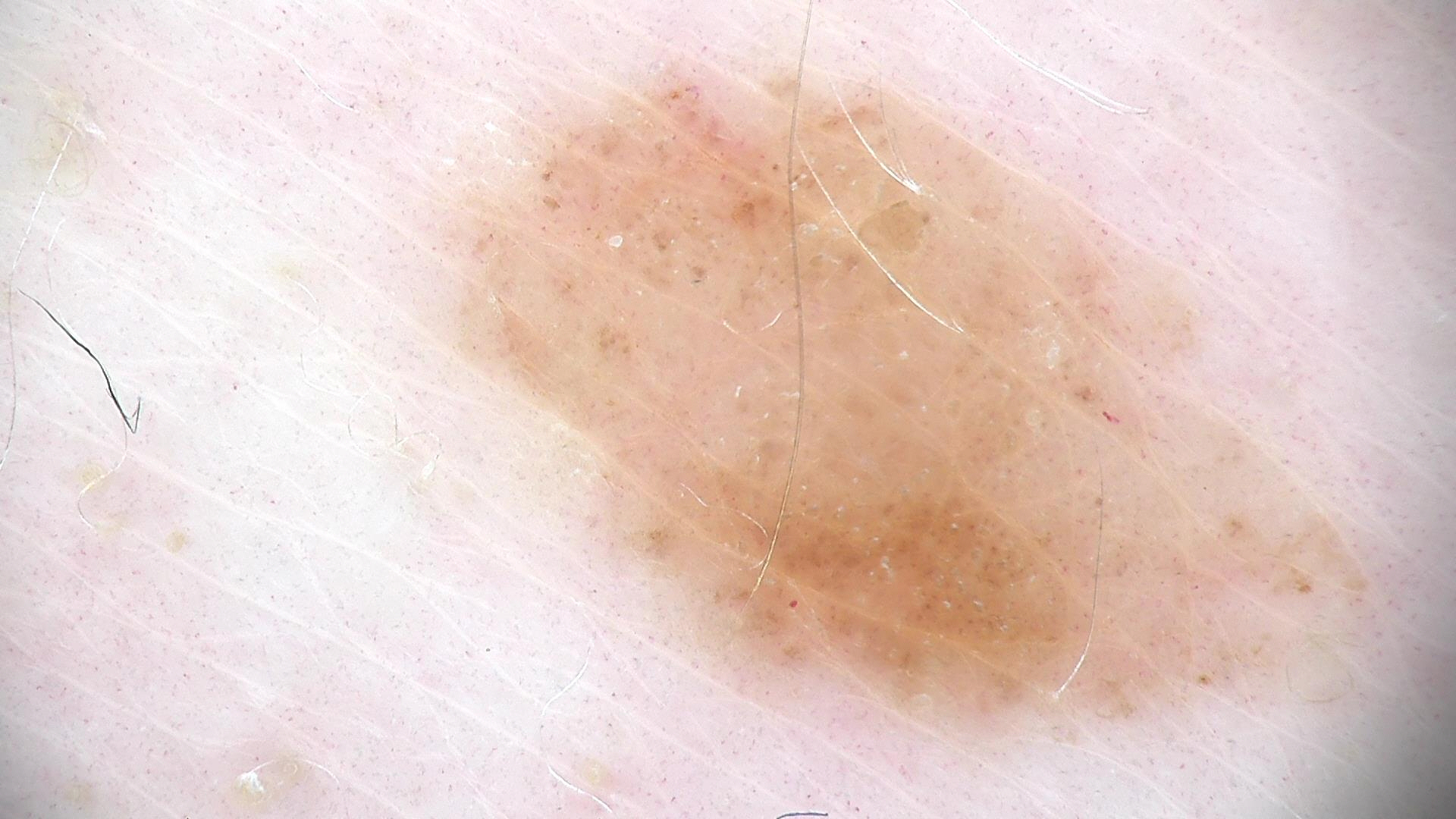image: dermoscopy; diagnosis: dysplastic junctional nevus (expert consensus).